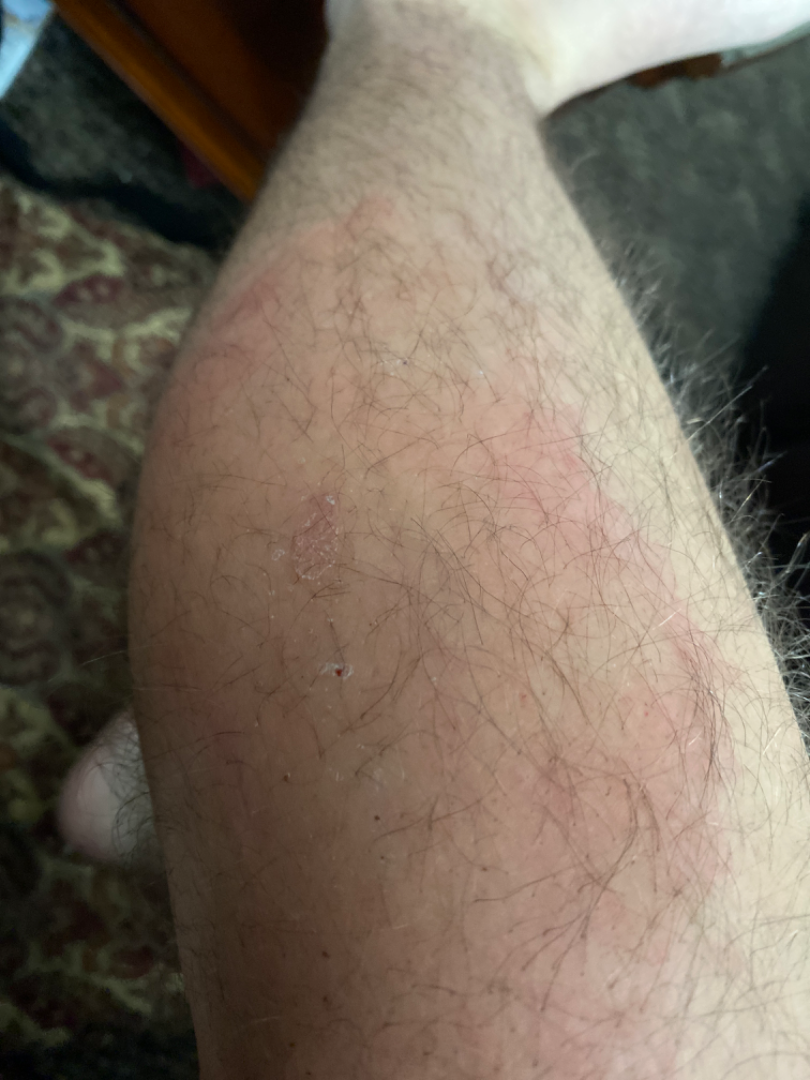Close-up view. Most likely Tinea; also on the differential is Eczema; a more distant consideration is Allergic Contact Dermatitis.